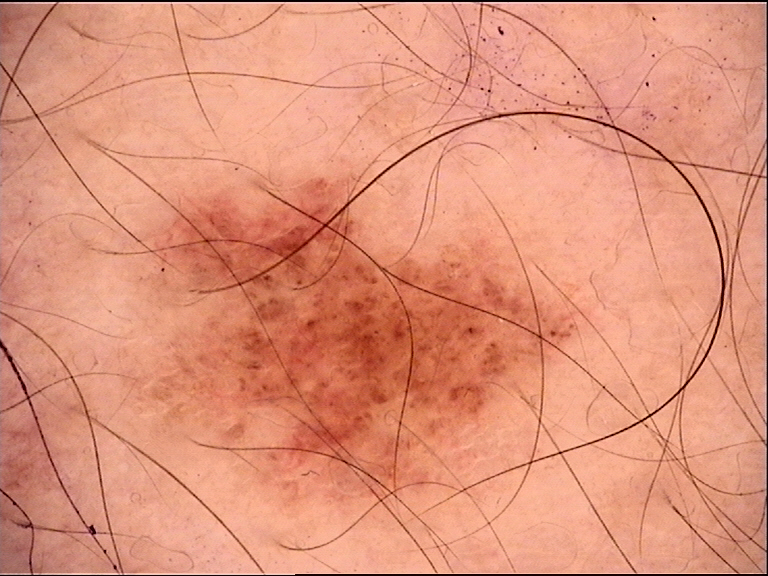A dermatoscopic image of a skin lesion.
Diagnosed as a dysplastic junctional nevus.